Located on the palm; the photograph is a close-up of the affected area; the contributor is 30–39, male — 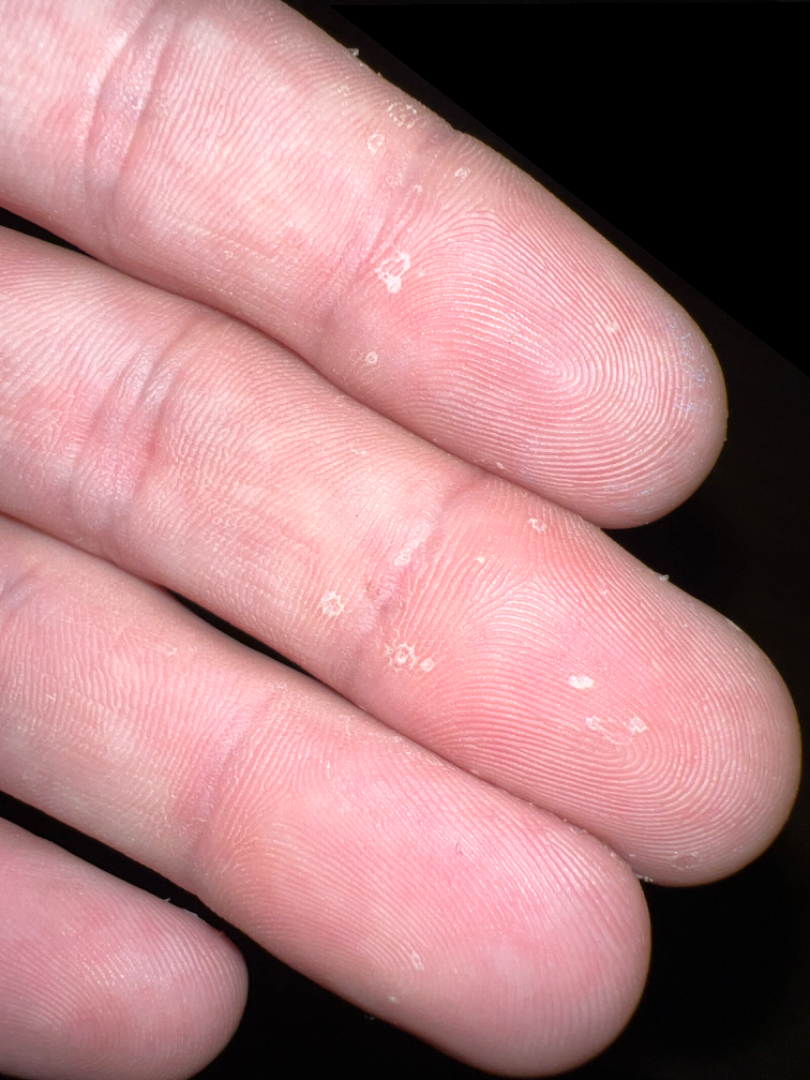Assessment:
The reviewing dermatologist was unable to assign a differential diagnosis from the image.
Clinical context:
The patient considered this acne. The condition has been present for about one day. Self-reported Fitzpatrick IV. The patient notes the lesion is rough or flaky.